A dermoscopic photograph of a skin lesion.
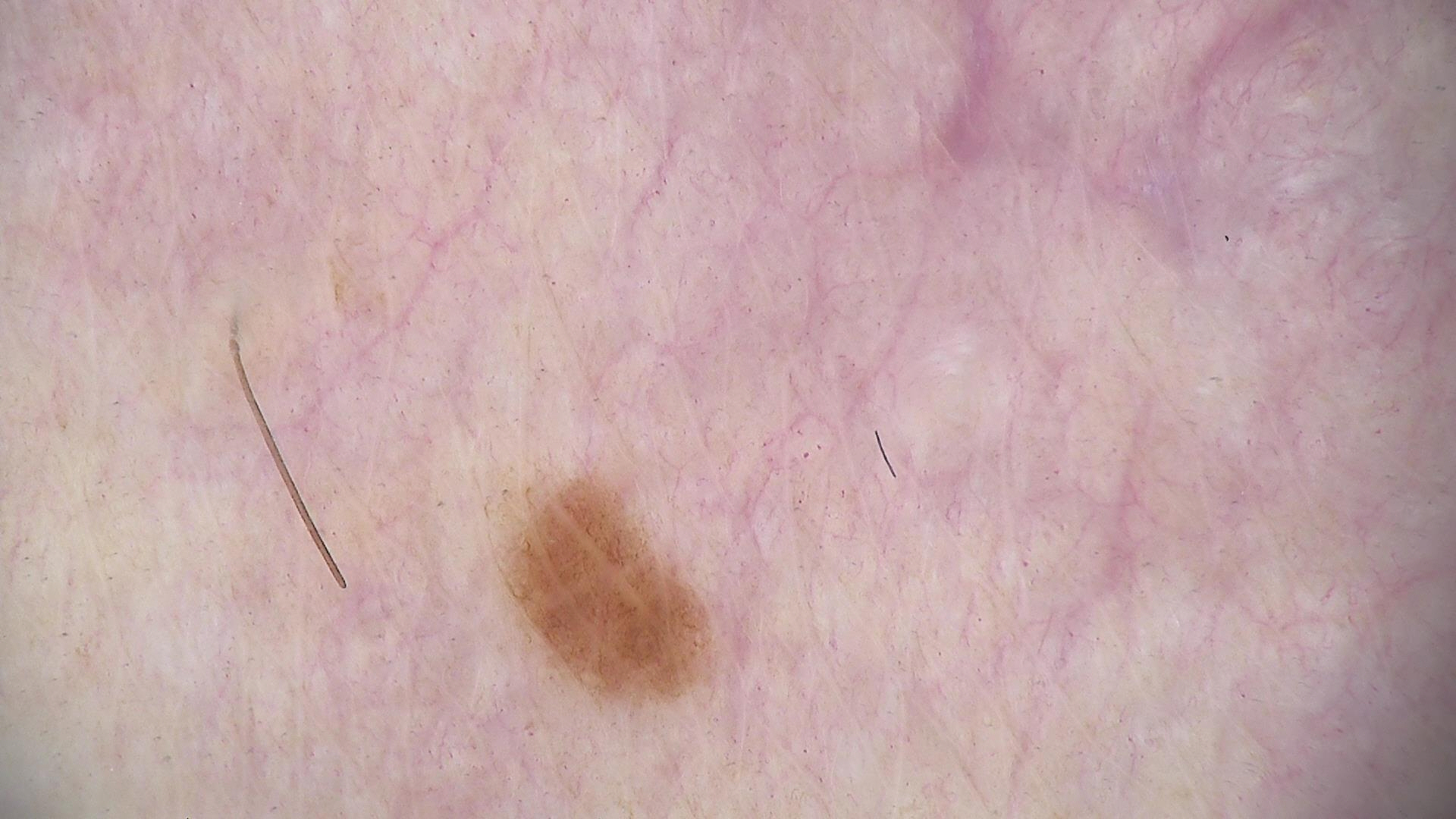diagnostic label = dysplastic junctional nevus (expert consensus).